A dermoscopic photograph of a skin lesion.
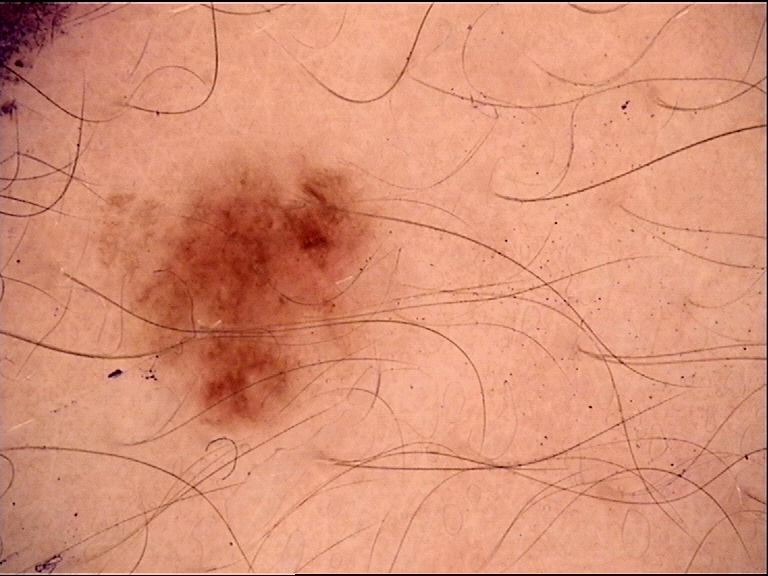Classified as a dysplastic junctional nevus.